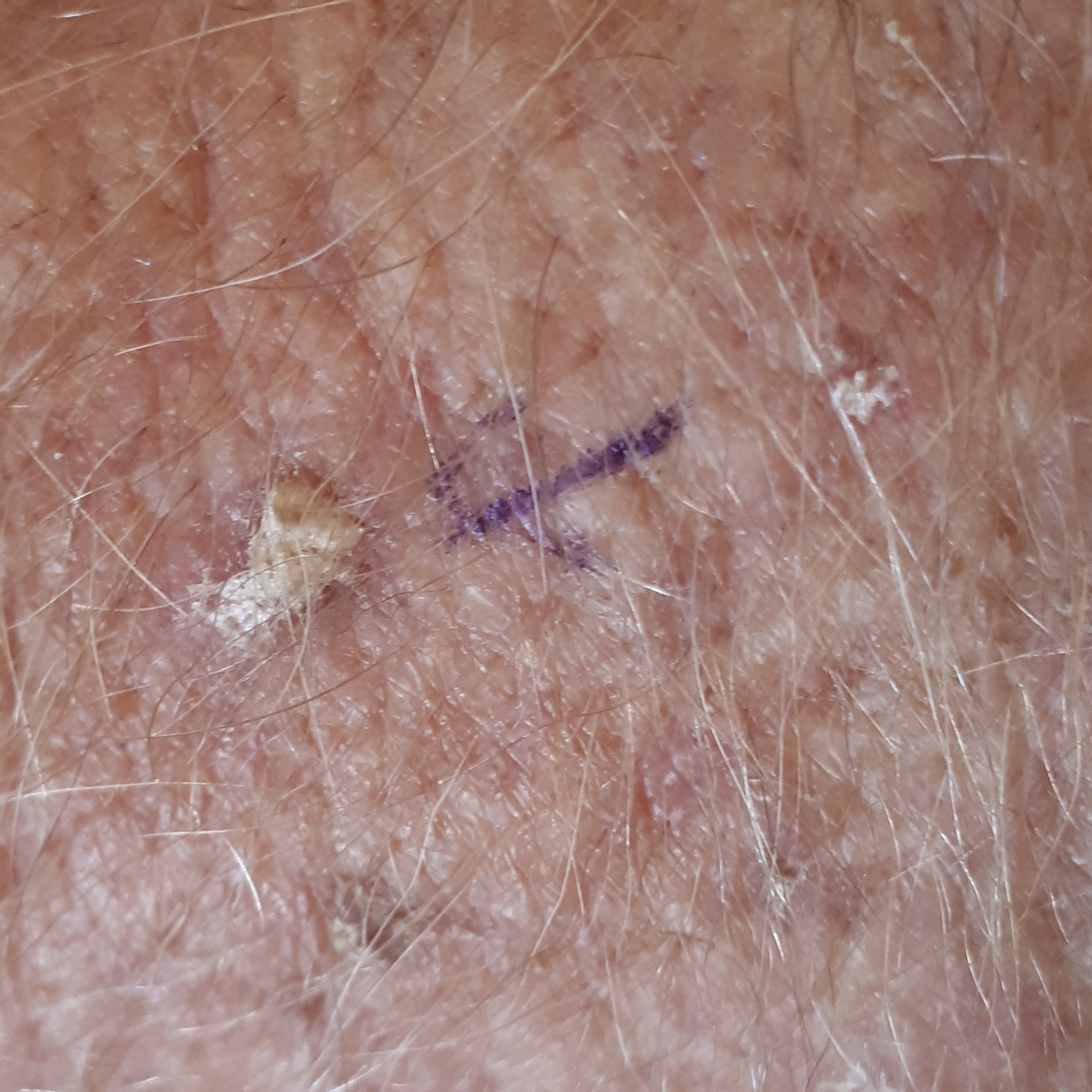Impression:
Clinically diagnosed as an actinic keratosis.